The photograph is a close-up of the affected area. The affected area is the leg — 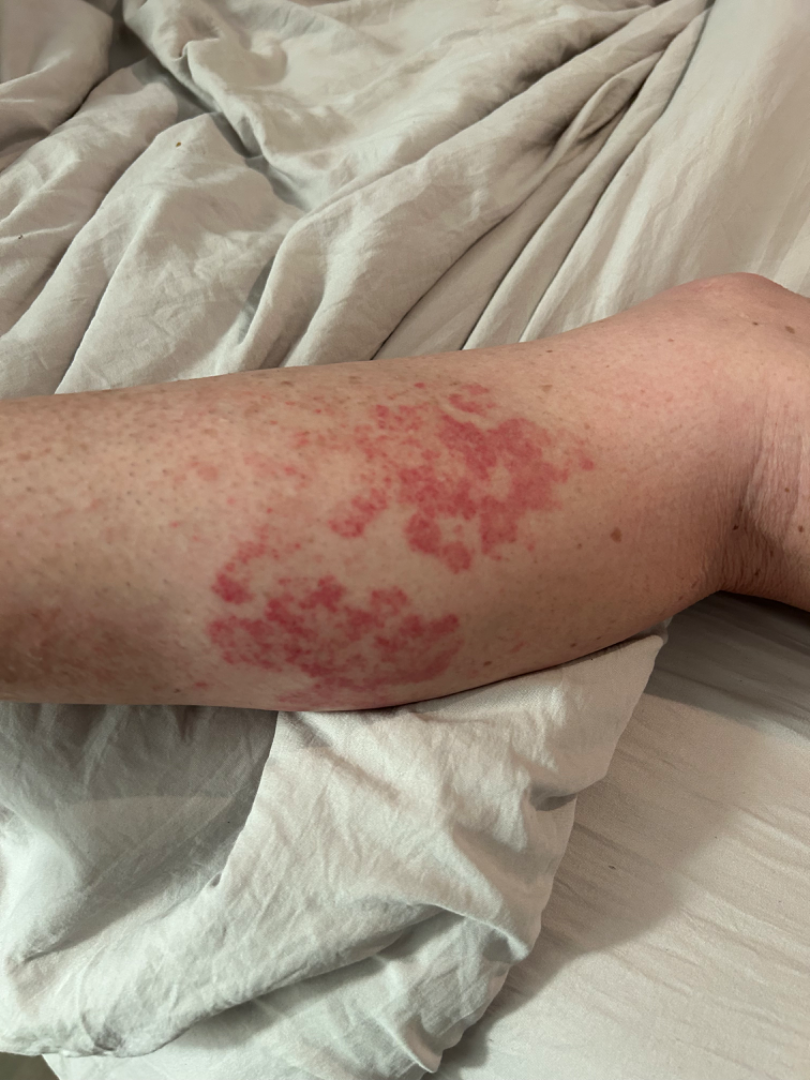On remote dermatologist review, in keeping with Leukocytoclastic Vasculitis.